A dermoscopy image of a skin lesion · a female patient aged 73 · the patient says their skin reddens with sun exposure · few moles overall by the patient's own estimate · collected as part of a research study, without a referral diagnosis:
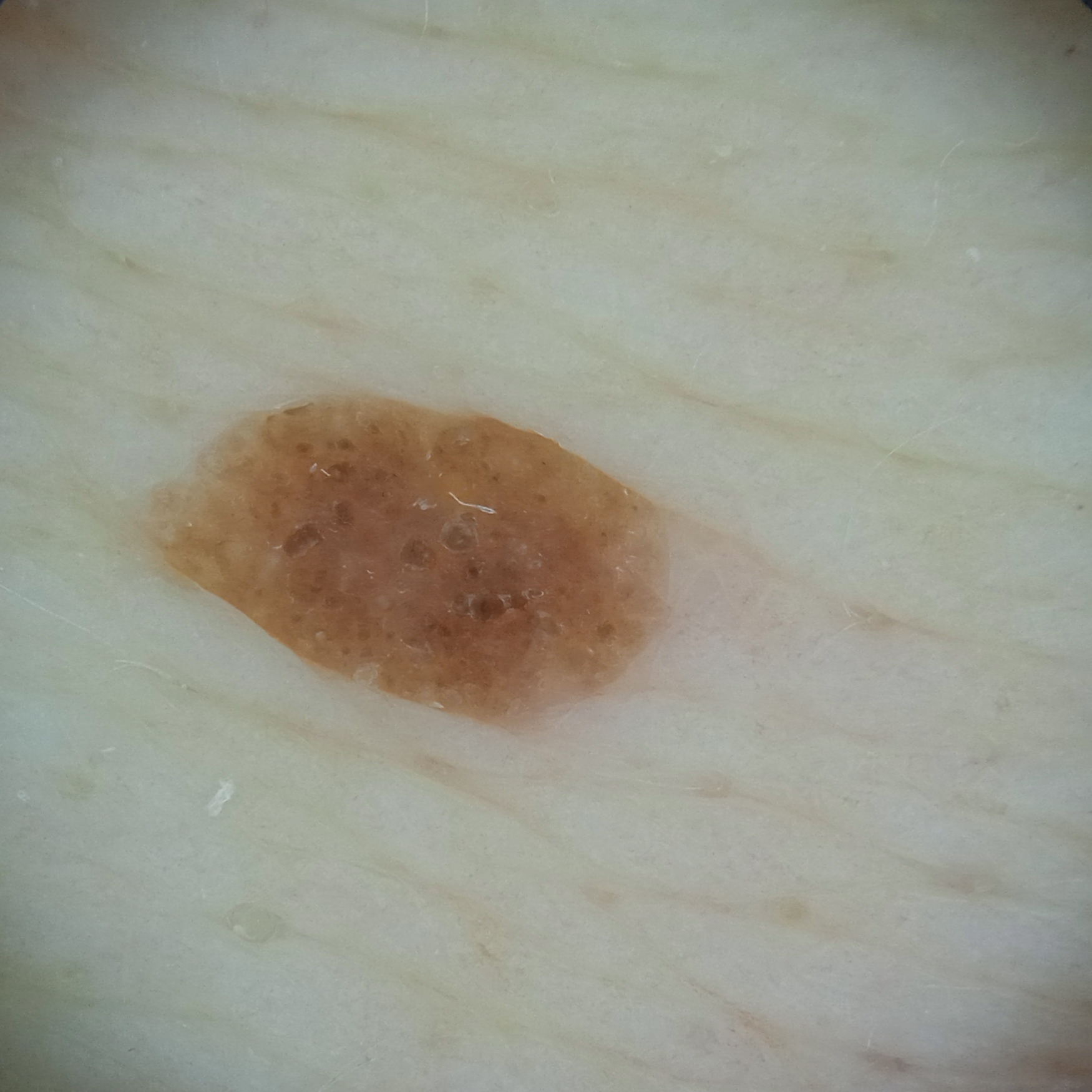– location: the back
– size: 6 mm
– assessment: seborrheic keratosis (dermatologist consensus)